The affected area is the back of the hand · self-categorized by the patient as a rash · the patient notes itching · the patient reported no systemic symptoms · this image was taken at a distance · the subject is 40–49, male · present for about one day · the patient notes the lesion is flat and raised or bumpy:
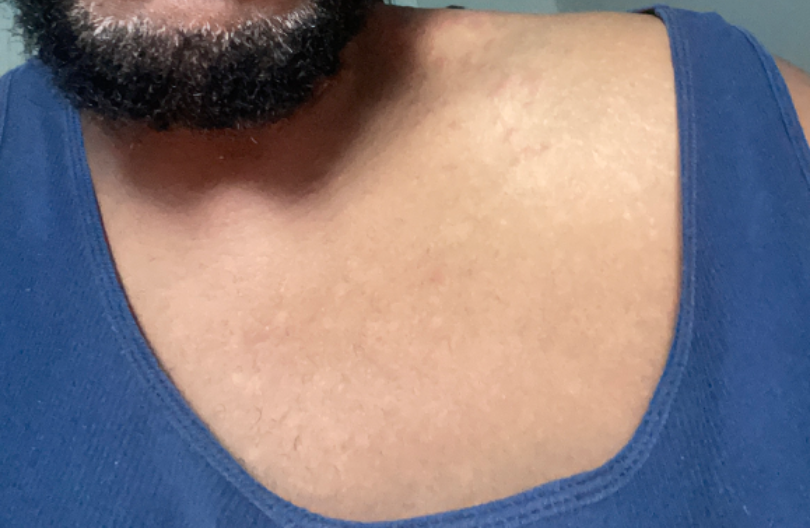Case summary:
• assessment — unable to determine